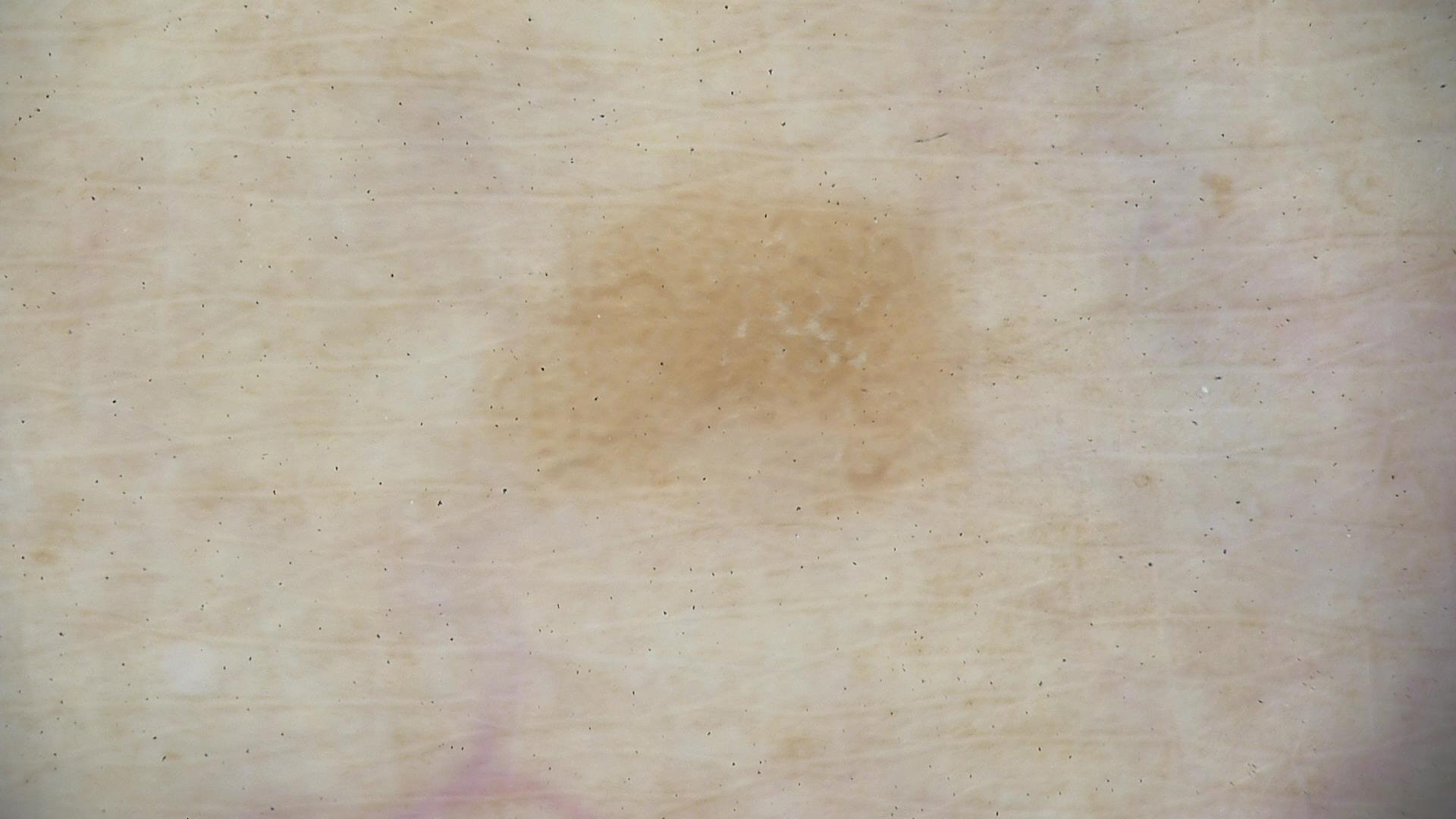Diagnosed as a keratinocytic, benign lesion — a seborrheic keratosis.